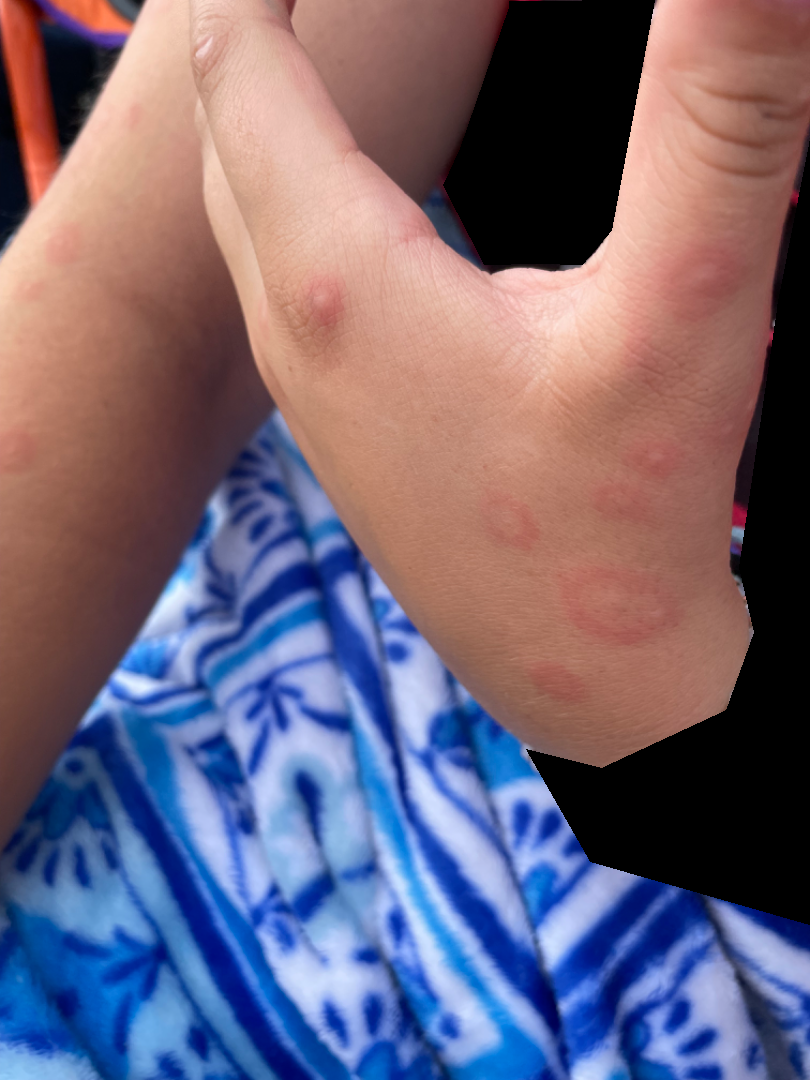symptom duration: one to four weeks; location: arm, palm and leg; patient: female, age 18–29; image framing: close-up; surface texture: raised or bumpy and fluid-filled; clinical impression: most consistent with Erythema multiforme.